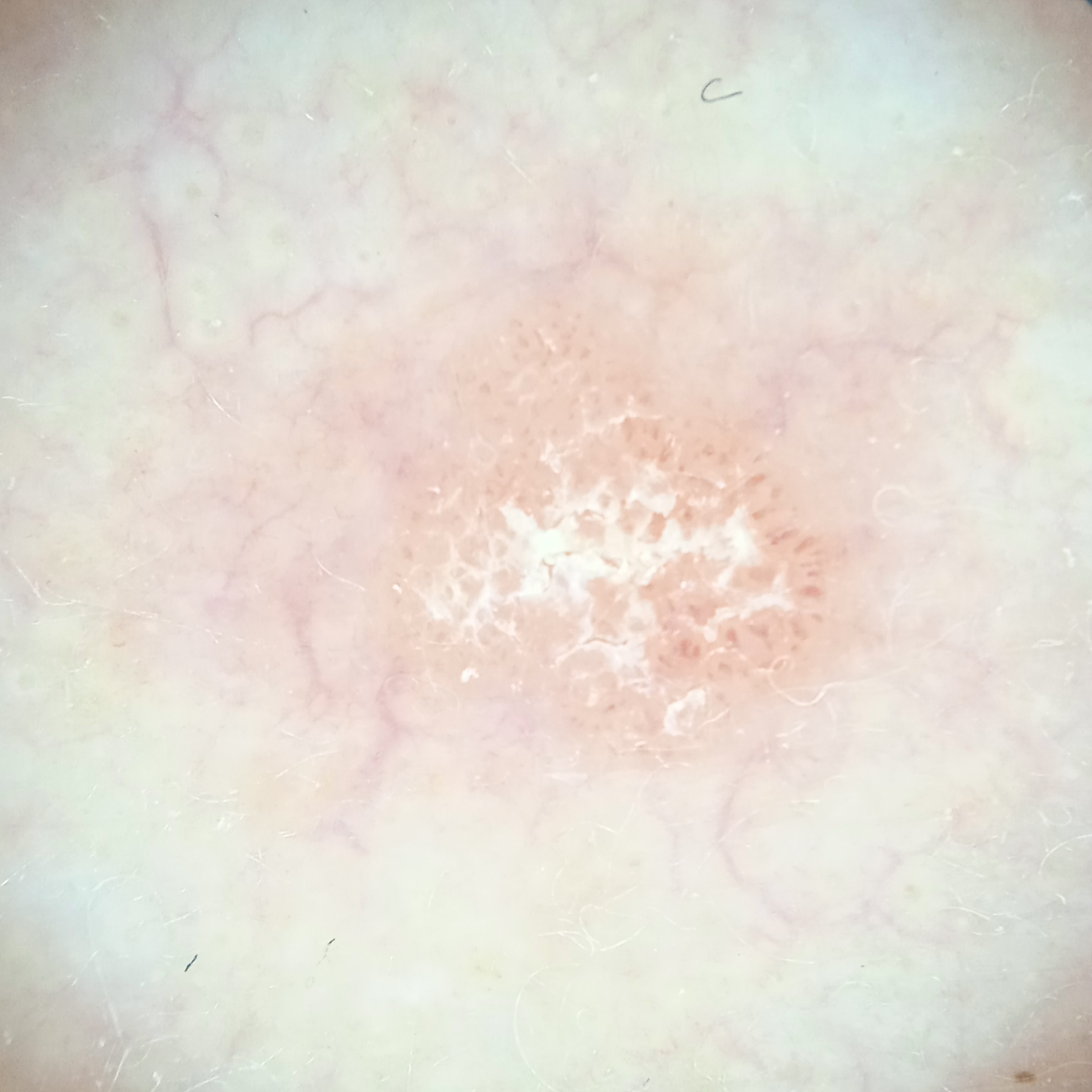{"diagnosis": {"name": "actinic keratosis", "malignancy": "benign"}}